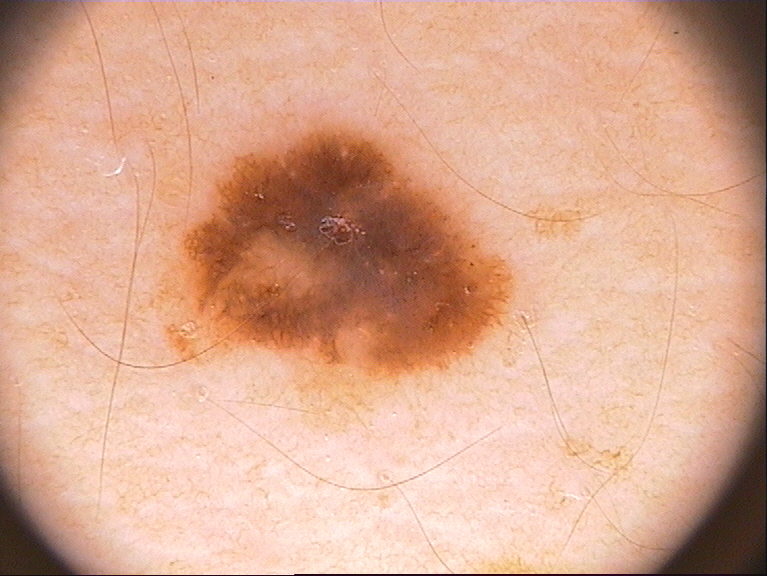– image type — dermatoscopic image of a skin lesion
– patient — male
– location — x1=156, y1=126, x2=517, y2=435
– dermoscopic features — pigment network and globules
– extent — moderate
– diagnostic label — a melanocytic nevus